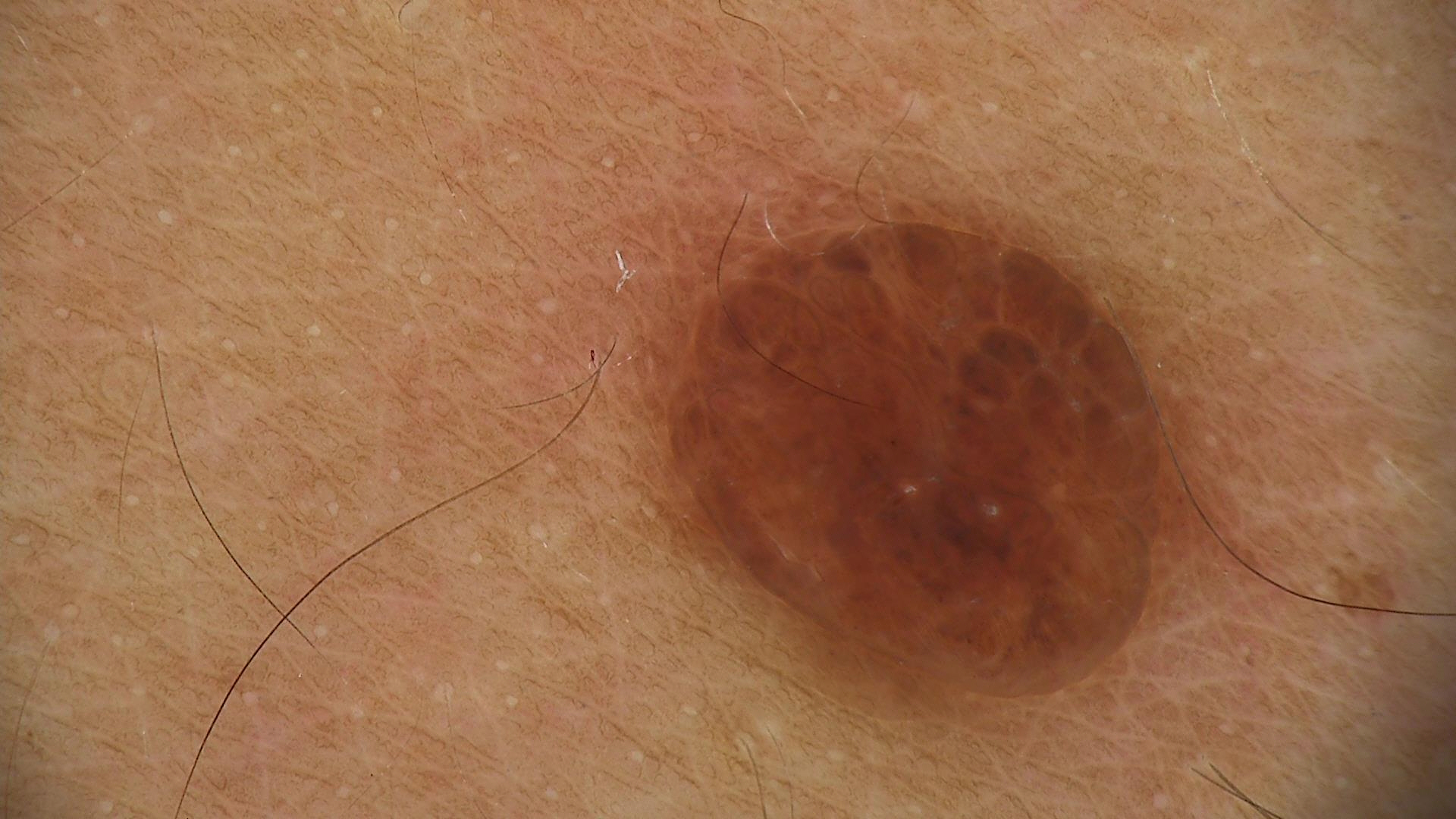A dermoscopy image of a single skin lesion.
The architecture is that of a banal lesion.
The diagnosis was a dermal nevus.